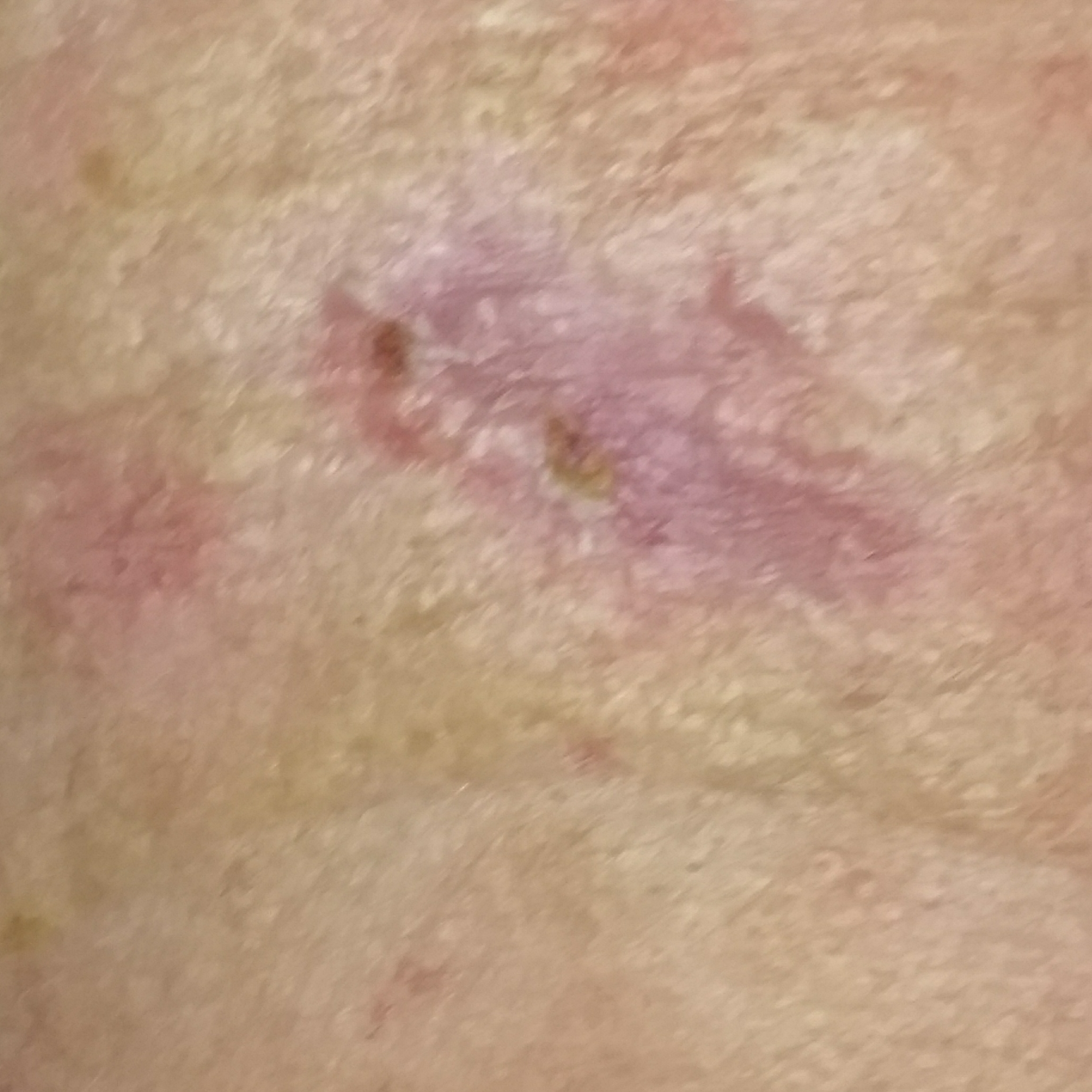A male patient age 77.
A clinical photo of a skin lesion taken with a smartphone.
The lesion was found on the face.
Histopathology confirmed a basal cell carcinoma.